Dermoscopy of a skin lesion.
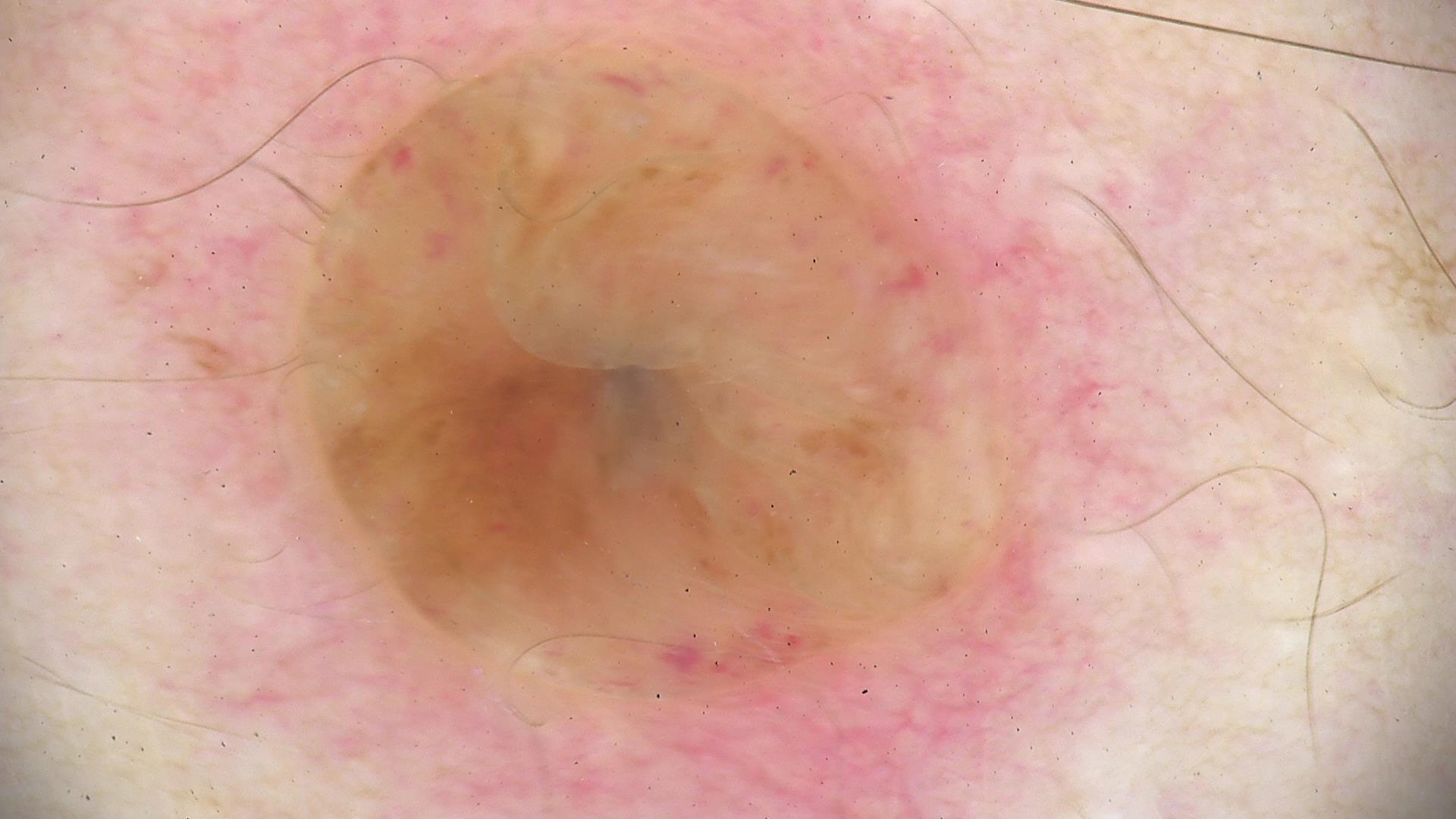Case: The morphology is that of a banal lesion. Conclusion: Diagnosed as a dermal nevus.